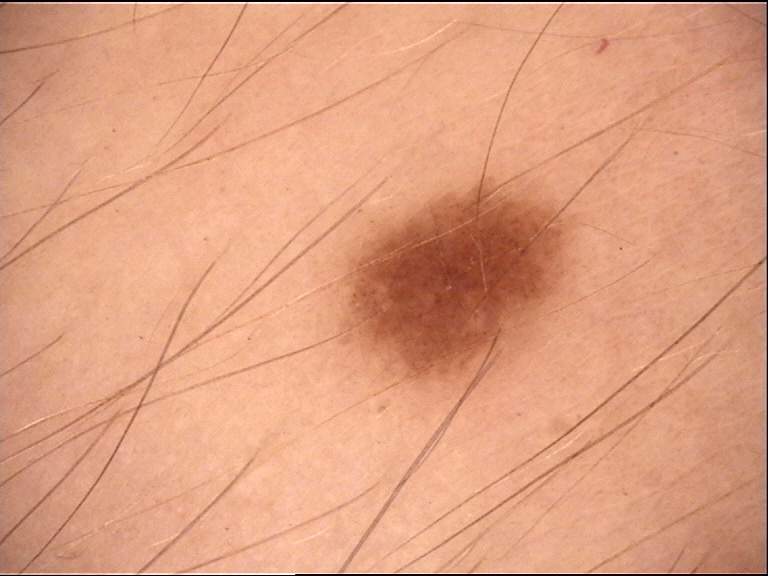{"image": "dermatoscopy", "diagnosis": {"name": "junctional nevus", "code": "jb", "malignancy": "benign", "super_class": "melanocytic", "confirmation": "expert consensus"}}